A skin lesion imaged with a dermatoscope: 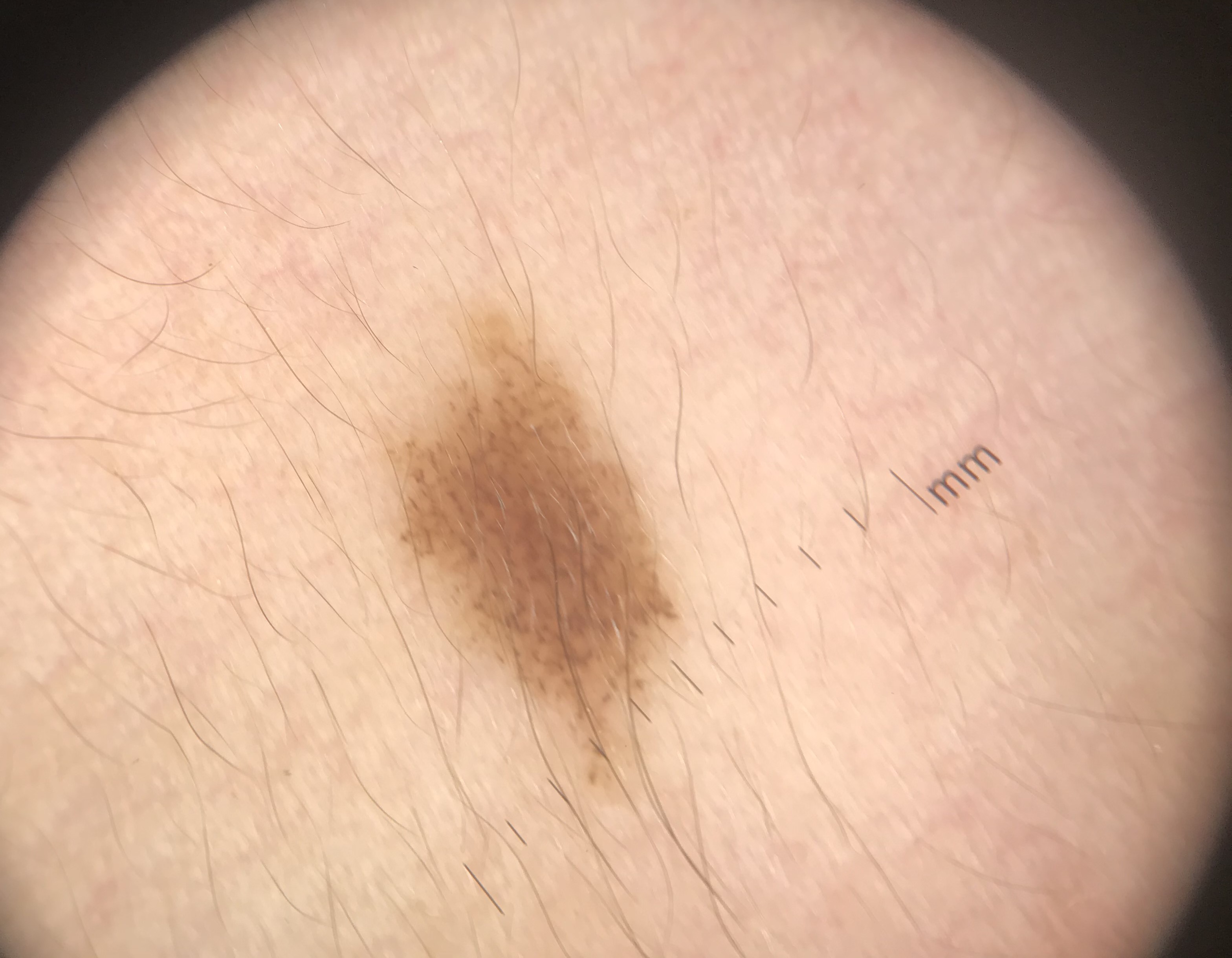diagnosis = dysplastic junctional nevus (expert consensus).